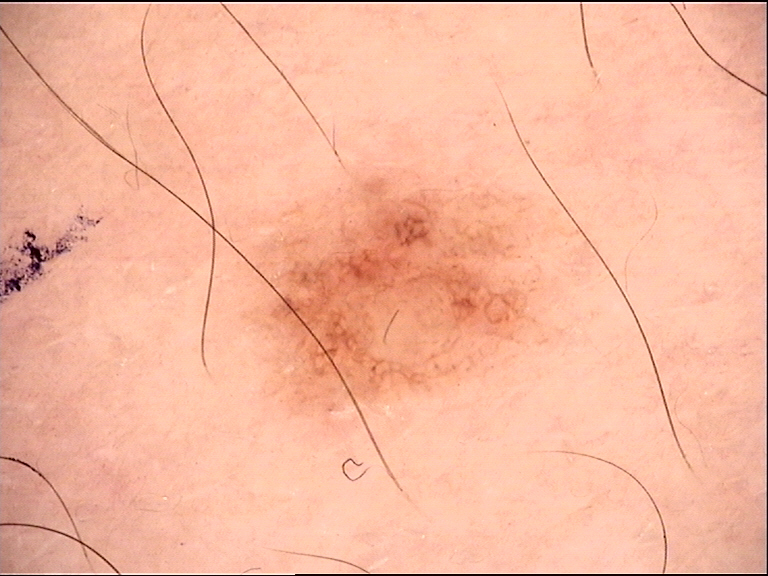diagnosis:
  name: dysplastic junctional nevus
  code: jd
  malignancy: benign
  super_class: melanocytic
  confirmation: expert consensus